A dermoscopic close-up of a skin lesion:
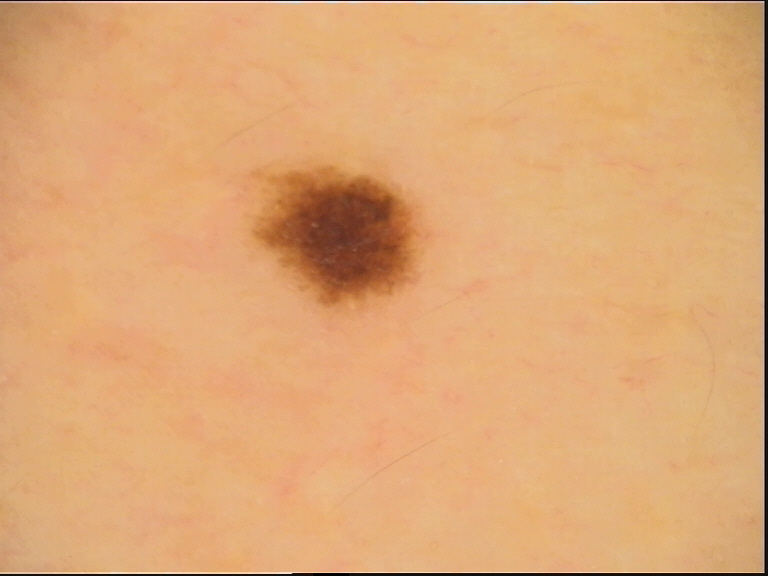Impression:
Classified as a benign lesion — a dysplastic junctional nevus.